The subject is a male aged 18–29. This is a close-up image. The affected area is the top or side of the foot:
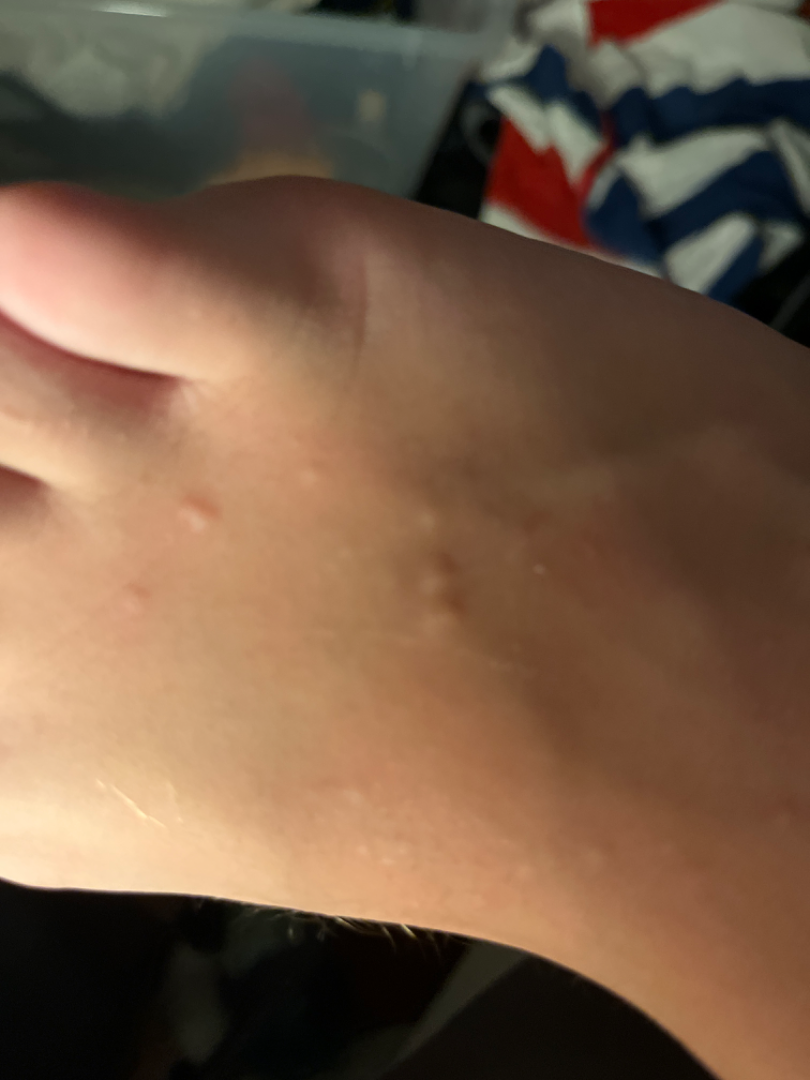<case>
<assessment>could not be assessed</assessment>
</case>